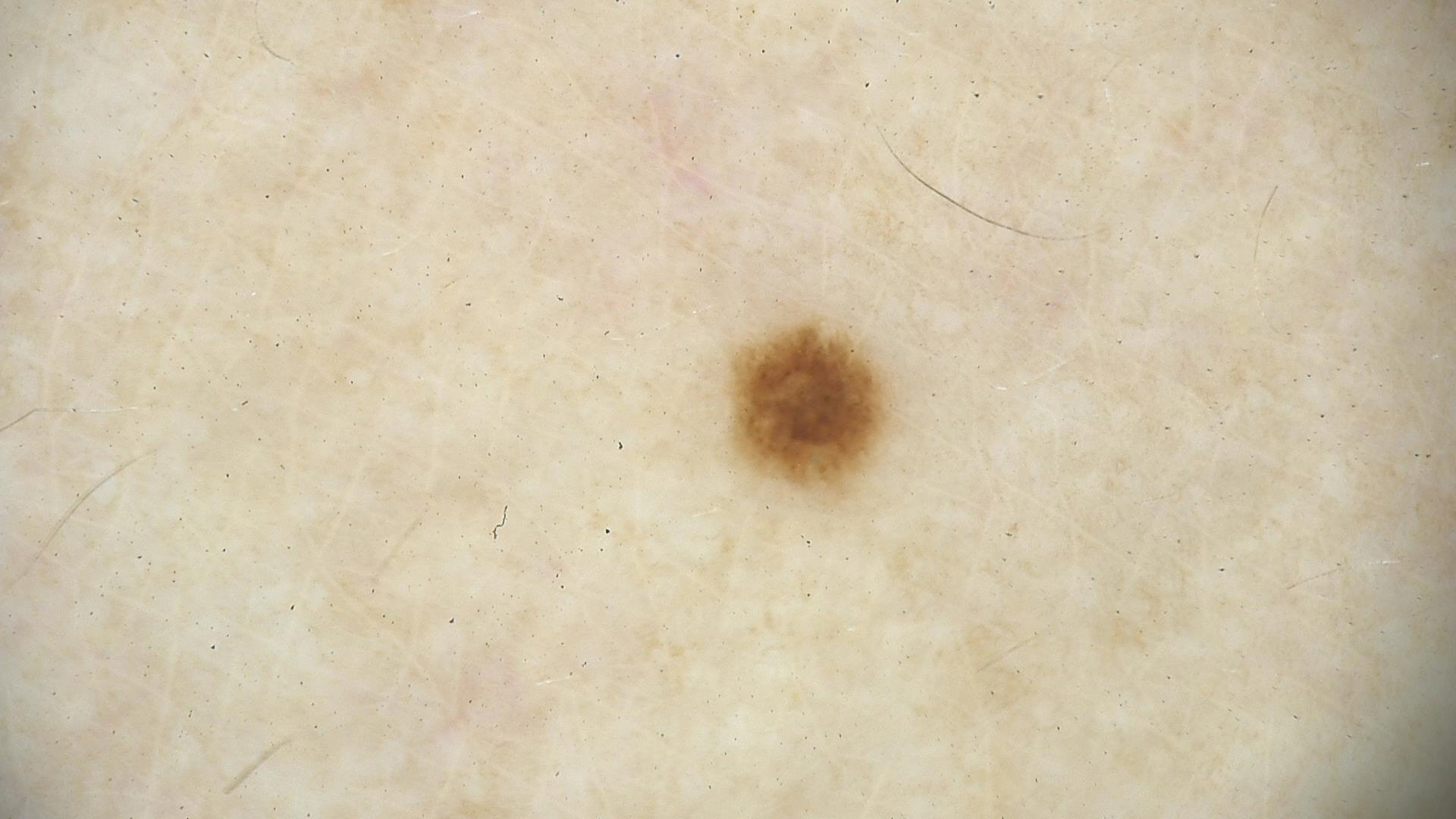– image type — dermatoscopy
– diagnosis — junctional nevus (expert consensus)